The front of the torso and back of the torso are involved · self-reported Fitzpatrick III; lay graders estimated a Monk Skin Tone of 4 · the patient notes the condition has been present for less than one week · the patient notes the lesion is raised or bumpy and fluid-filled · the patient considered this a rash · no relevant systemic symptoms · the patient is 30–39, male · symptoms reported: pain, itching and burning · a close-up photograph:
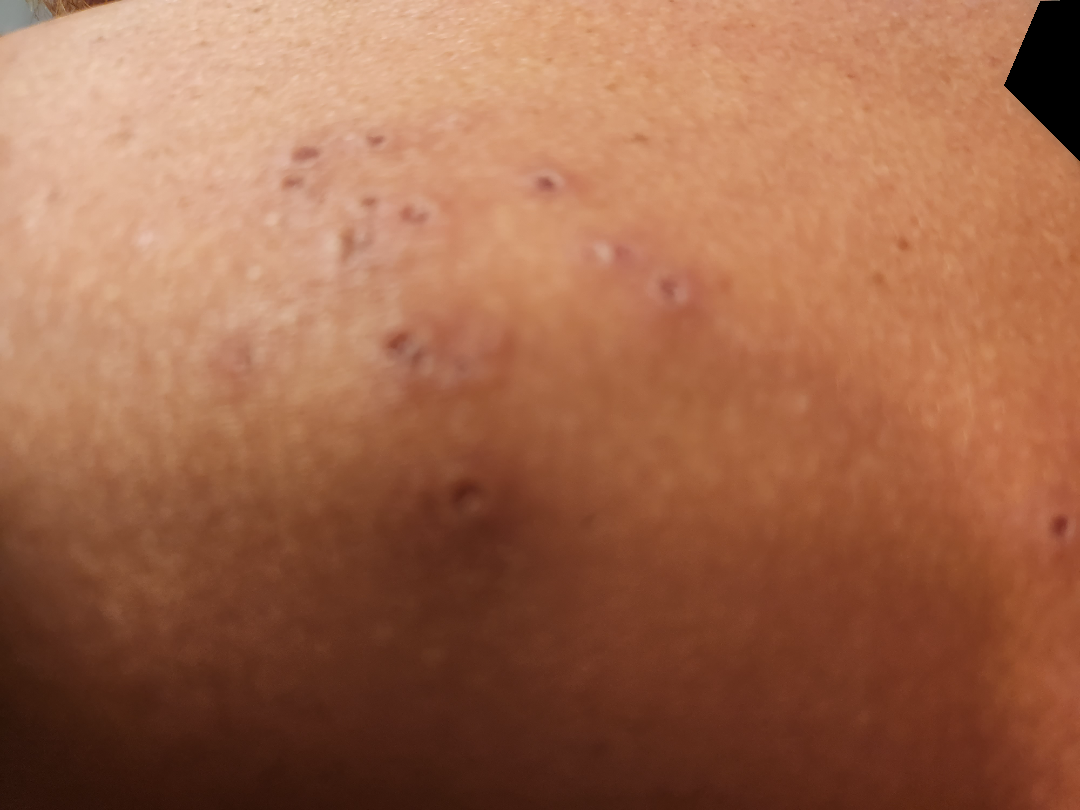The skin condition could not be confidently assessed from this image.